A female subject 32 years of age · a moderate number of moles by the patient's own estimate · a skin lesion imaged with a dermatoscope · by self-report, a personal history of cancer and a personal history of skin cancer.
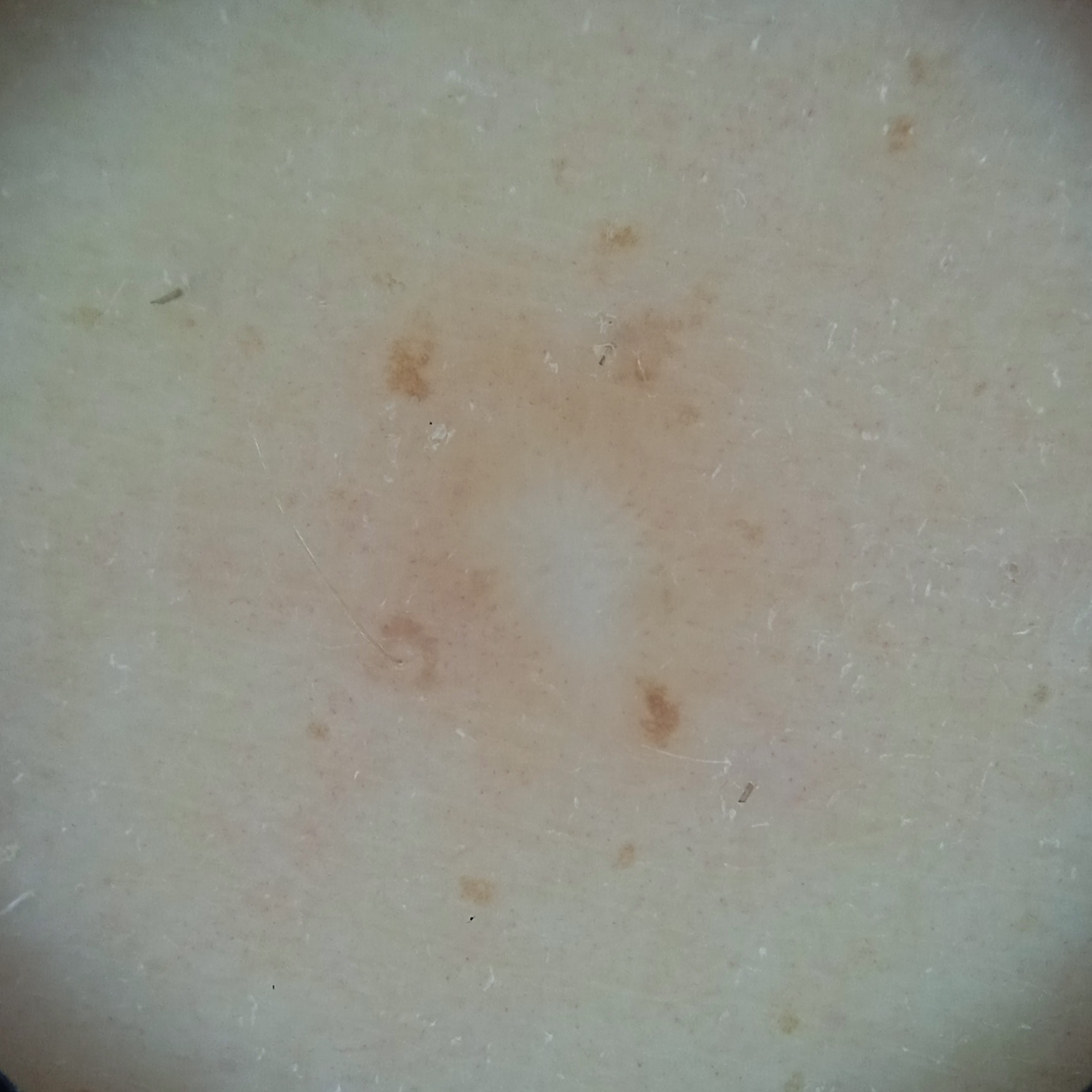Clinical context: The lesion involves a leg. Measuring roughly 5.4 mm. Conclusion: Four dermatologists reviewed the lesion; the consensus was a dermatofibroma; the reviewers were fairly confident; the differential also included a histiocytoma.